Reported lesion symptoms include itching and burning · the affected area is the arm and leg · the photograph was taken at a distance · texture is reported as raised or bumpy · the patient considered this a rash · the condition has been present for one to four weeks · no associated systemic symptoms reported · skin tone: Fitzpatrick skin type IV.
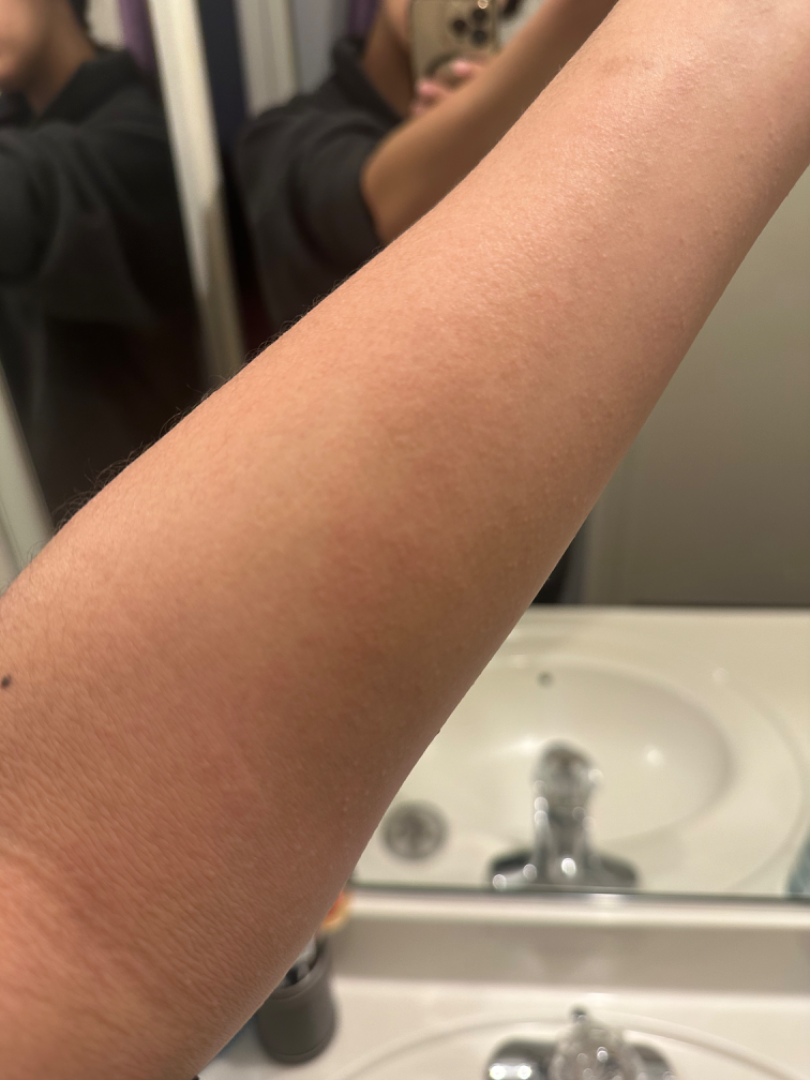On remote review of the image, Drug Rash, Viral Exanthem and Hypersensitivity were considered with similar weight.